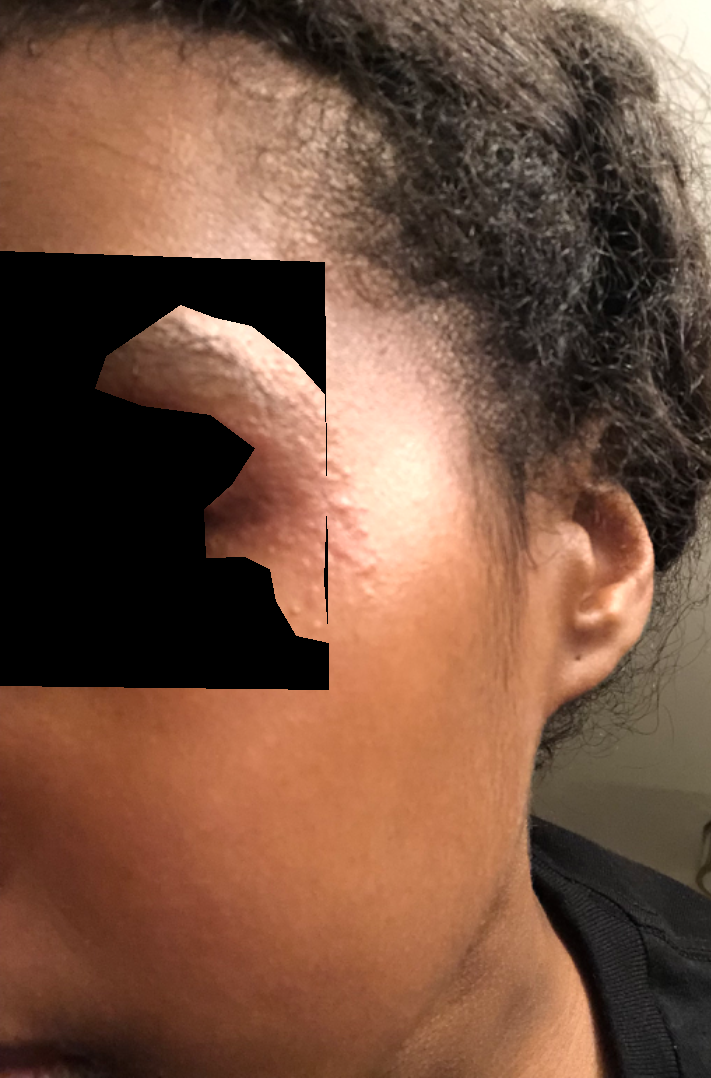assessment: ungradable on photographic review | contributor: female, age 18–29 | symptom duration: less than one week | texture: raised or bumpy | shot type: close-up | associated systemic symptoms: none reported | body site: head or neck | symptoms: bothersome appearance and enlargement.